Located on the leg, head or neck, arm, back of the torso and front of the torso · this image was taken at an angle.
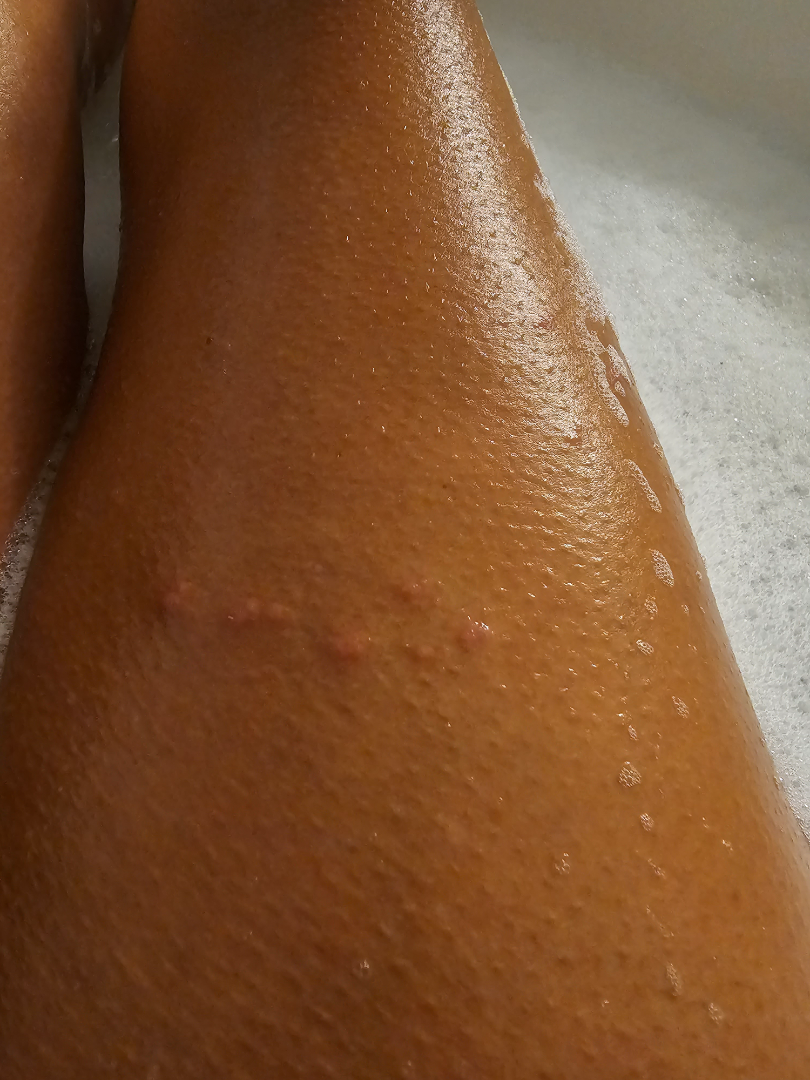Q: Texture?
A: raised or bumpy
Q: How does the patient describe it?
A: skin that appeared healthy to them
Q: What is the dermatologist's impression?
A: the favored diagnosis is Verruca vulgaris; also raised was SK/ISK; possibly Molluscum Contagiosum